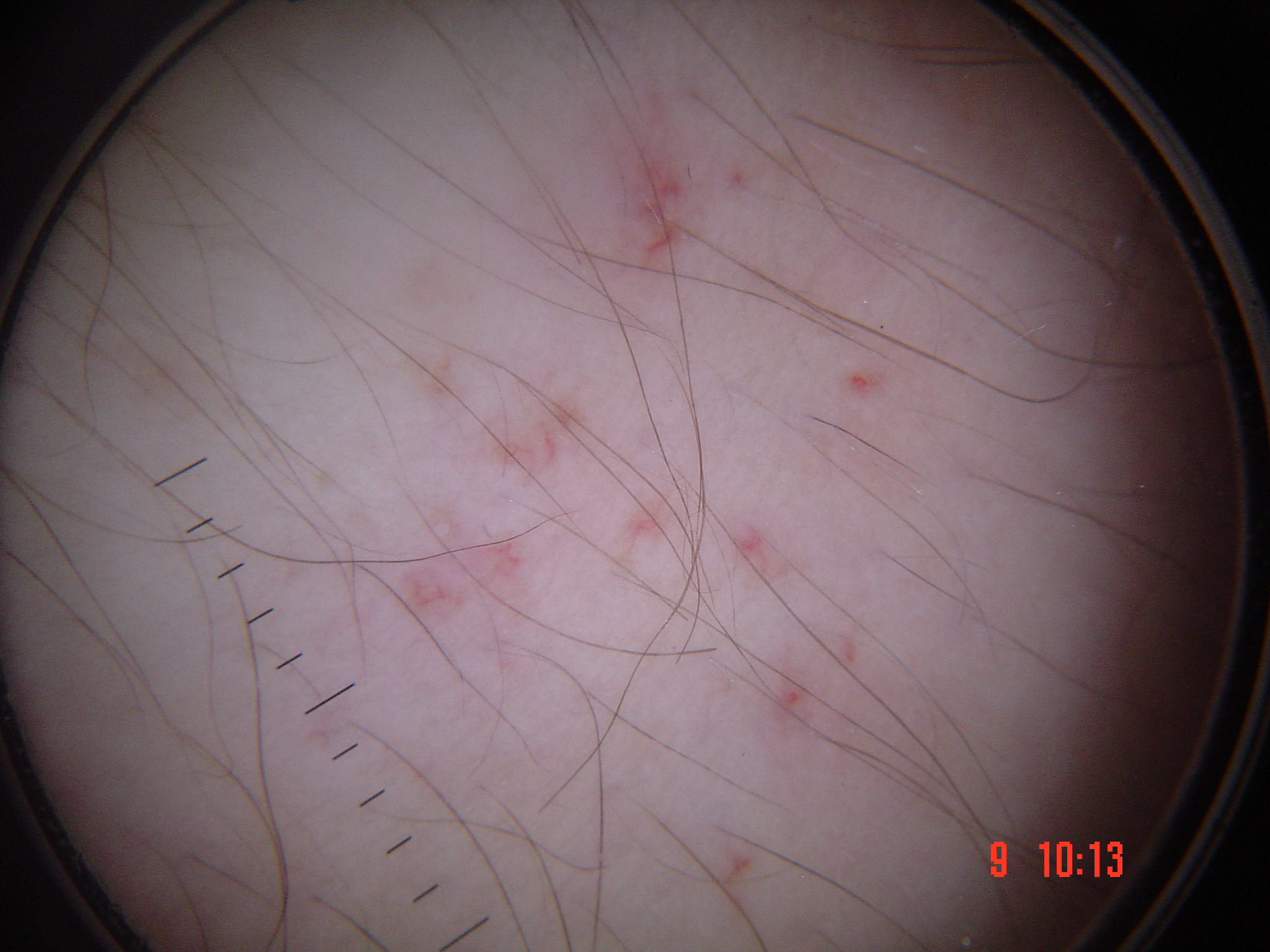Dermoscopy of a skin lesion.
Classified as a vascular lesion — a spider angioma.